A dermatoscopic image of a skin lesion:
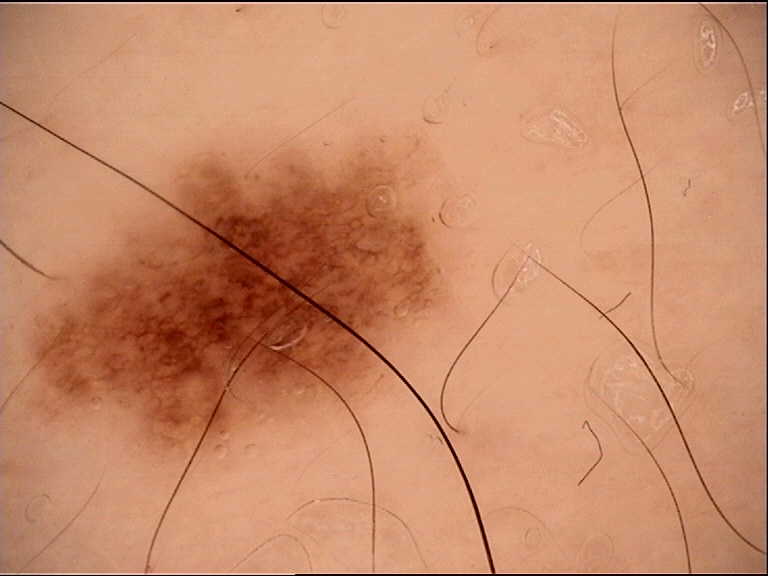Consistent with a dysplastic junctional nevus.